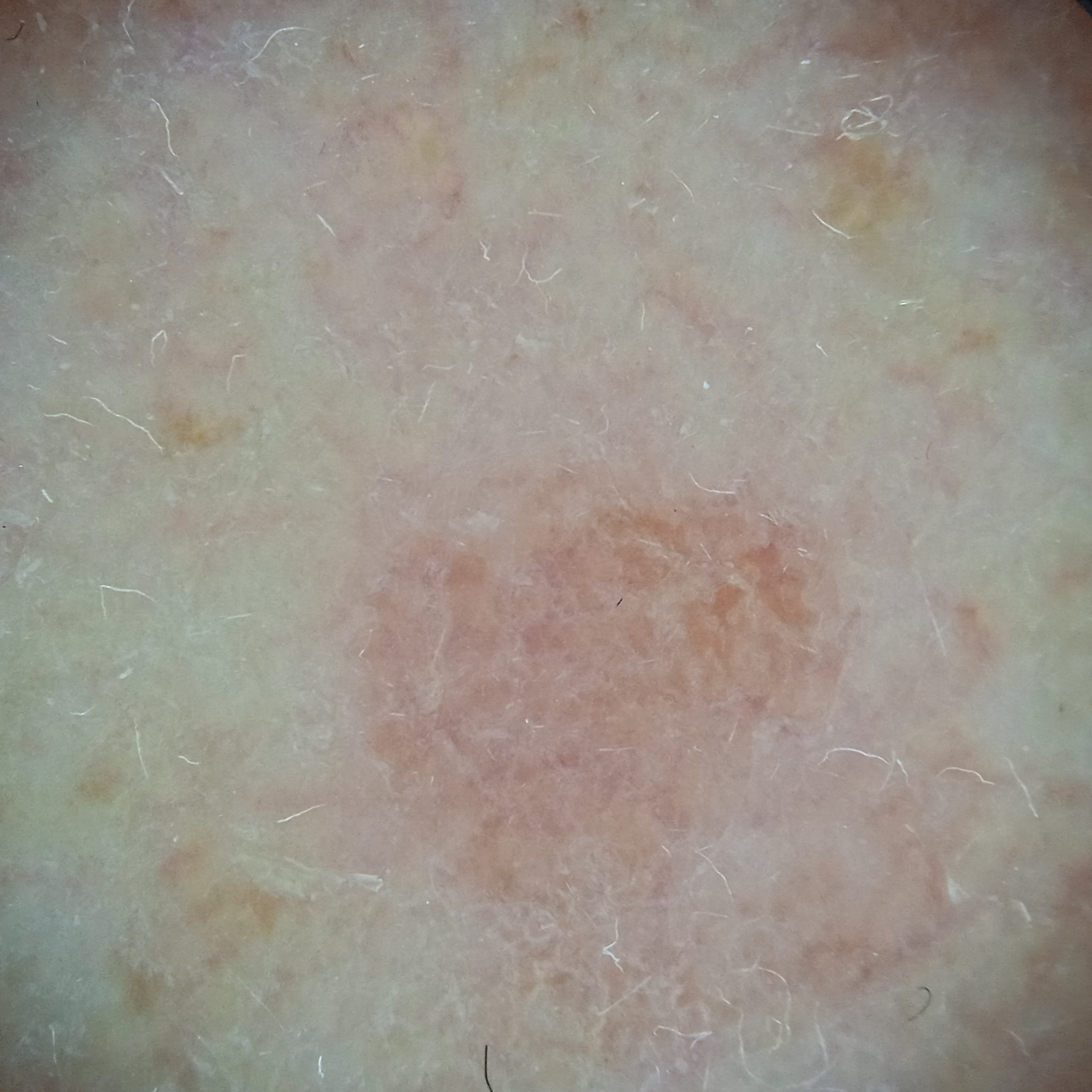The lesion was assessed as an actinic keratosis.